The contributor reports the lesion is raised or bumpy. The condition has been present for less than one week. The affected area is the top or side of the foot, leg and arm. The photo was captured at an angle: 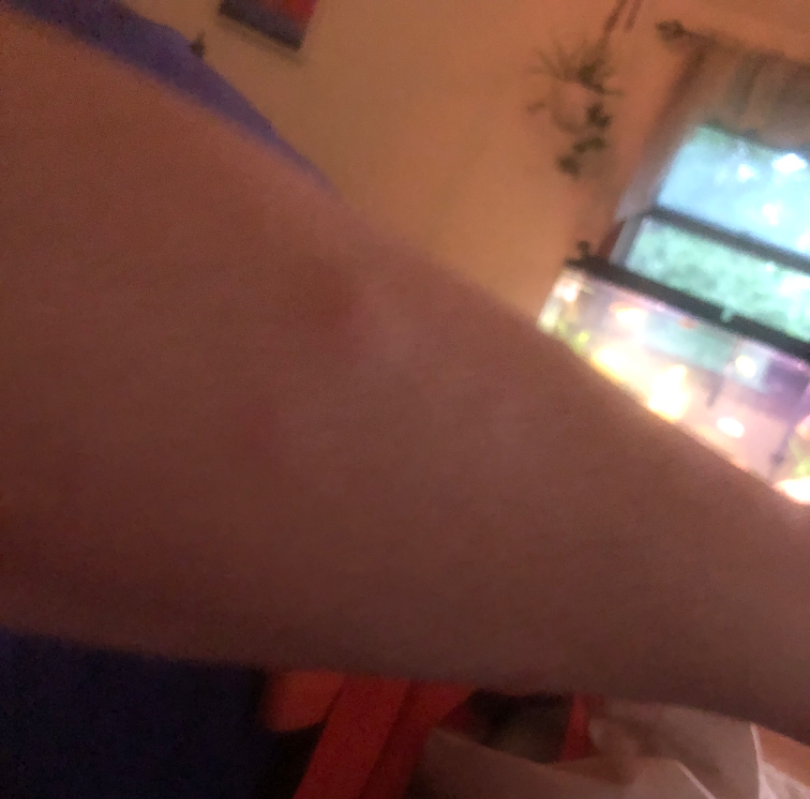Q: Could the case be diagnosed?
A: not assessable